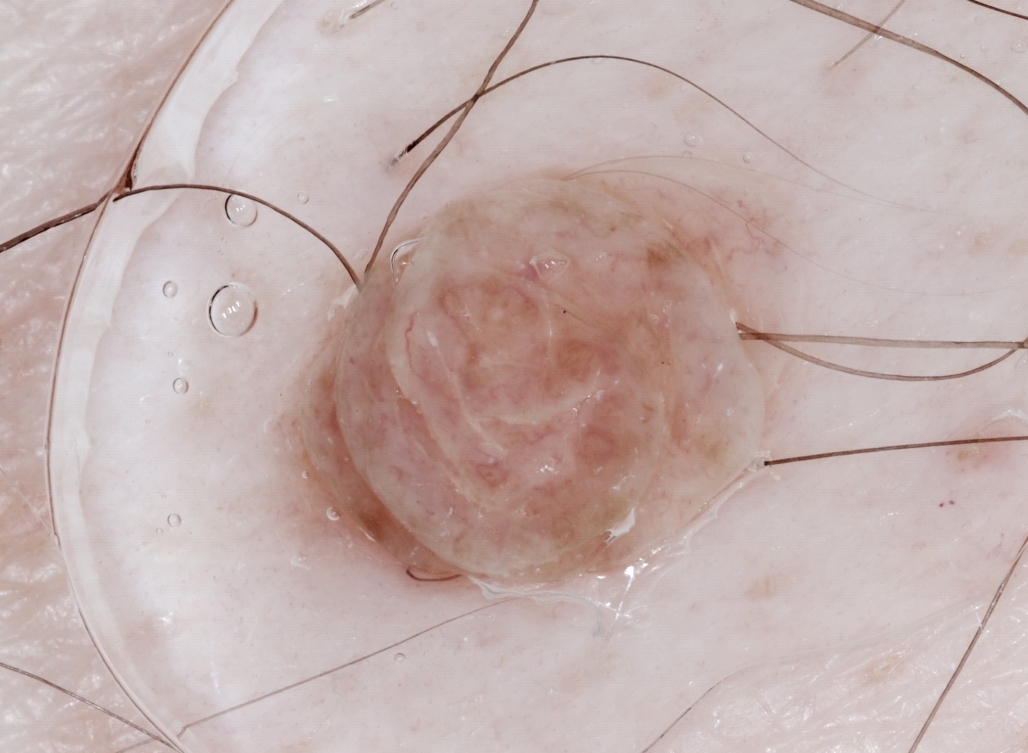This is a dermoscopic photograph of a skin lesion.
A male subject, roughly 65 years of age.
Dermoscopic assessment notes no negative network, streaks, milia-like cysts, or pigment network.
With coordinates (x1, y1, x2, y2), the lesion spans [274, 148, 809, 599].
The lesion was assessed as a melanocytic nevus.